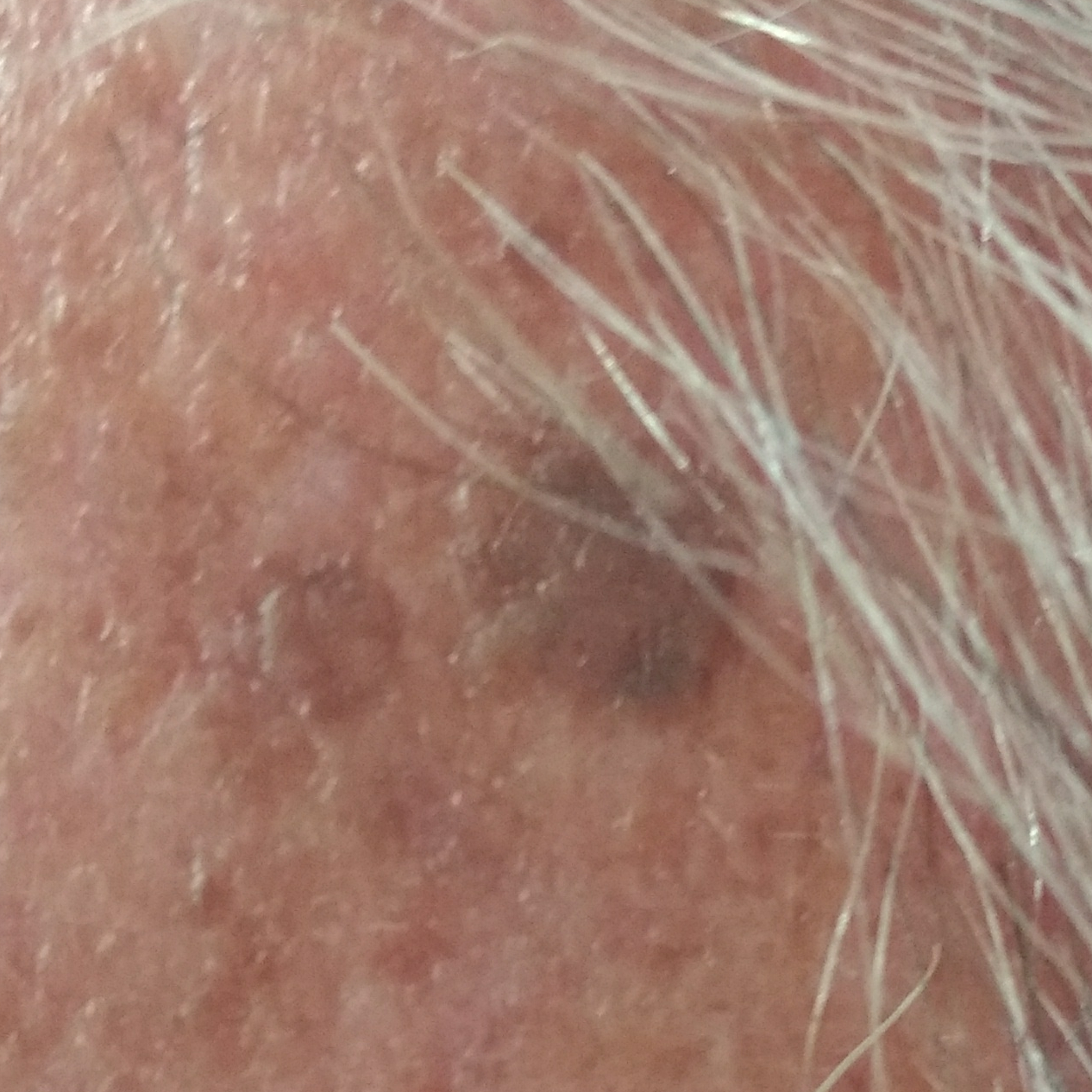By the patient's account, the lesion itches and is elevated, but does not hurt and has not changed.
Expert review favored a seborrheic keratosis.